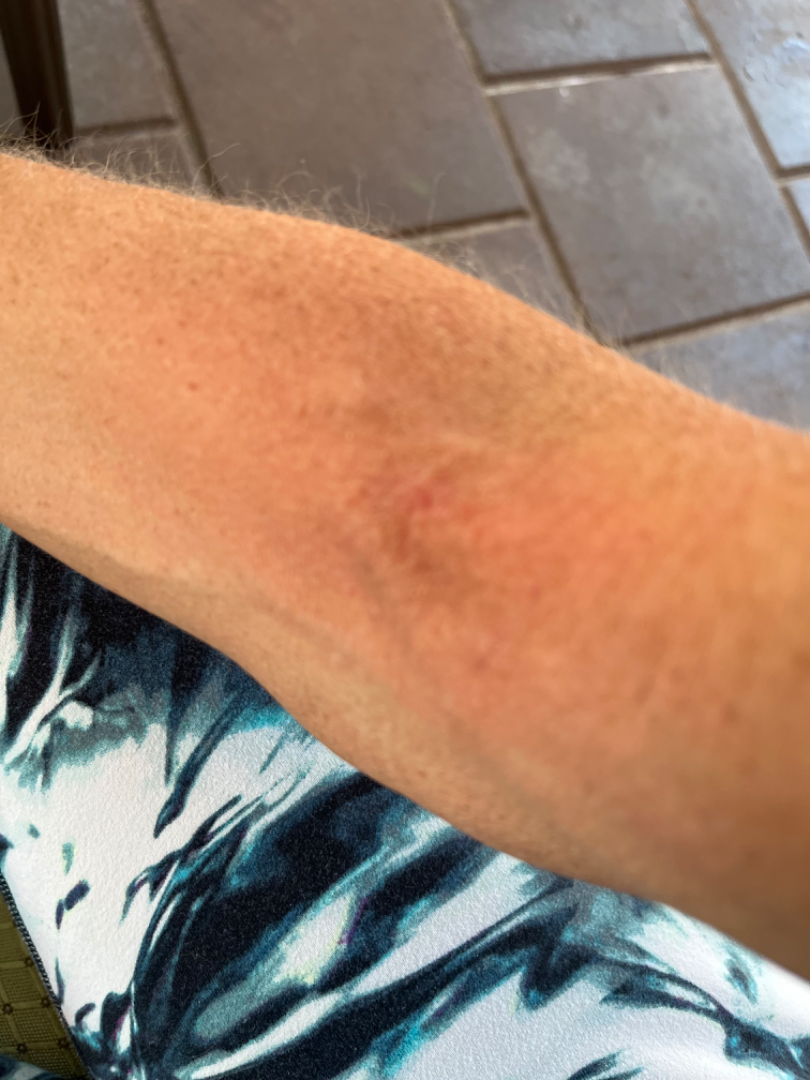History:
The contributor reports associated mouth sores. The photograph is a close-up of the affected area. The lesion is described as flat and raised or bumpy. Female patient, age 40–49. The patient considered this a rash. Reported duration is one to four weeks. The affected area is the back of the torso, arm, front of the torso and head or neck.
Impression:
The reviewing dermatologist's impression was: consistent with Eczema.